A dermoscopic image of a skin lesion.
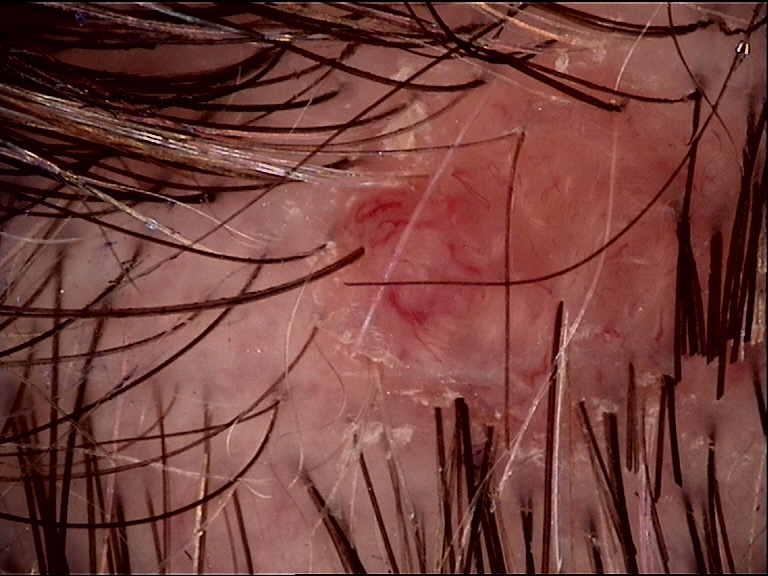diagnostic label: dermal nevus (expert consensus).